Dermoscopy of a skin lesion.
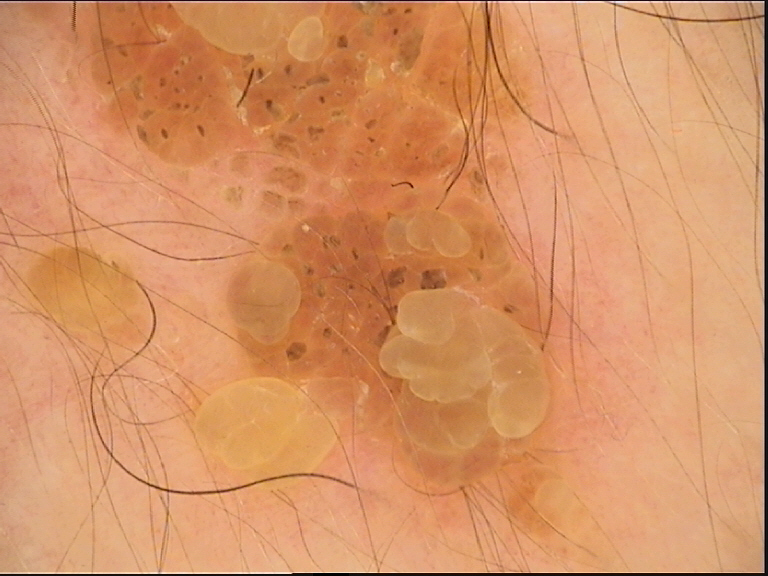Conclusion:
Labeled as a keratinocytic lesion — a seborrheic keratosis.